The arm is involved. An image taken at an angle — 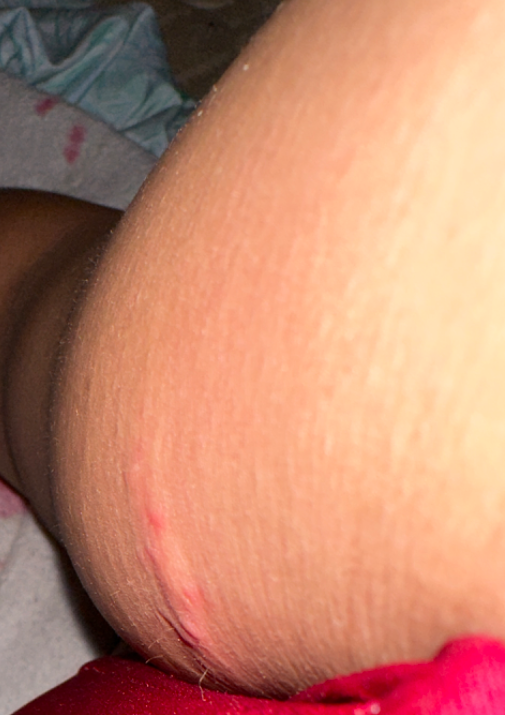Findings: Insect Bite and Herpes Simplex were each considered, in no particular order.